This image was taken at an angle; reported duration is one to four weeks; the lesion is described as fluid-filled and raised or bumpy; the contributor is 40–49, female; symptoms reported: bothersome appearance, pain, bleeding, itching and enlargement; located on the front of the torso, arm and leg.
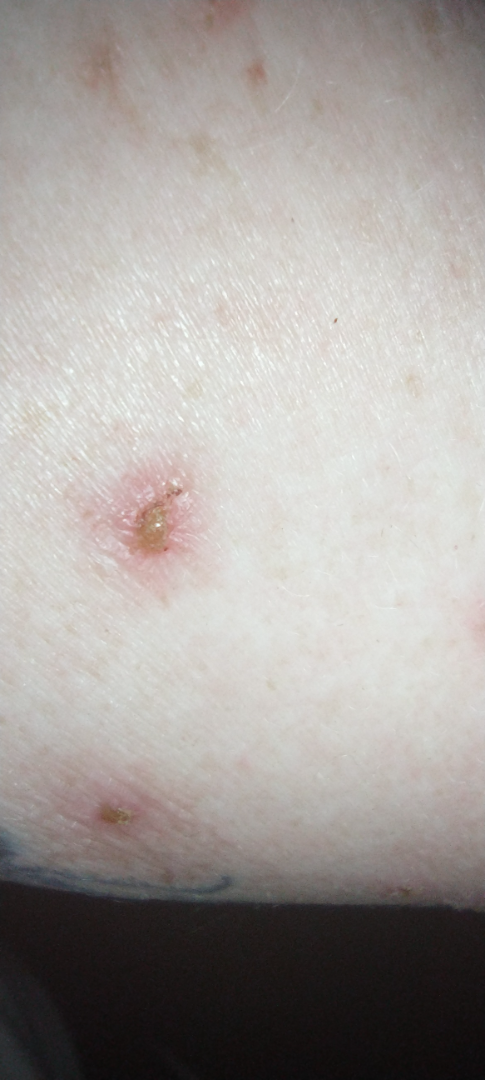  differential:
    leading:
      - Impetigo
    considered:
      - Abrasion, scrape, or scab